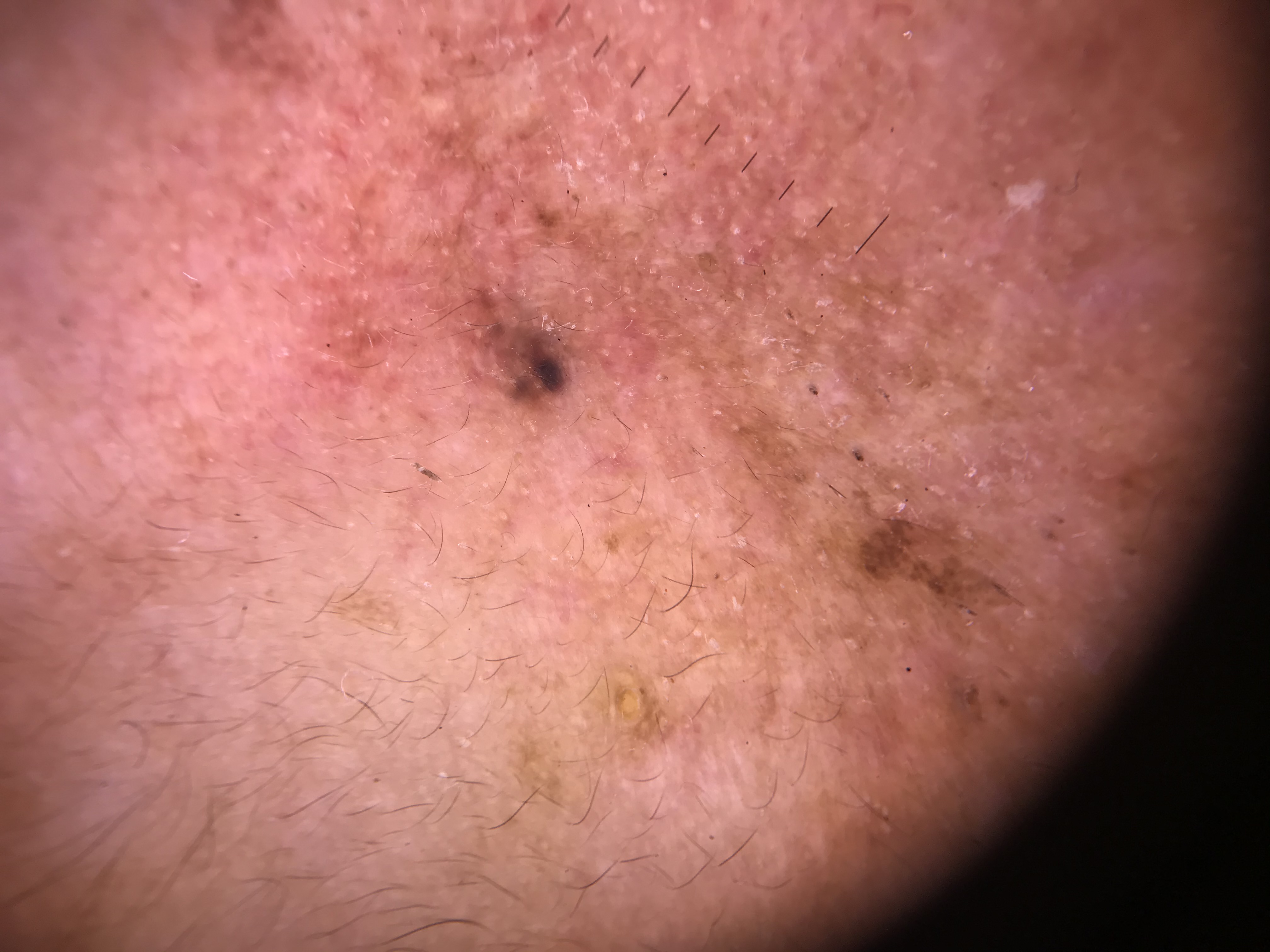Case:
A dermoscopic image of a skin lesion.
Diagnosis:
Histopathology confirmed a malignant lesion — a basal cell carcinoma.